By history, alcohol use, pesticide exposure, prior skin cancer (patient or family), no tobacco use, and no prior malignancy (patient or family) · a clinical close-up photograph of a skin lesion · a male subject 70 years of age · skin type II: 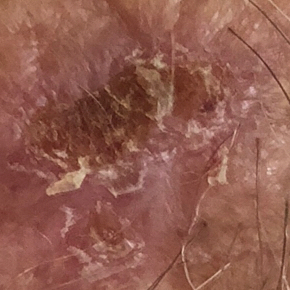Patient and lesion: The lesion measures 15 × 11 mm. The patient reports that the lesion itches, but is not elevated and does not hurt. Pathology: Biopsy-confirmed as a basal cell carcinoma.